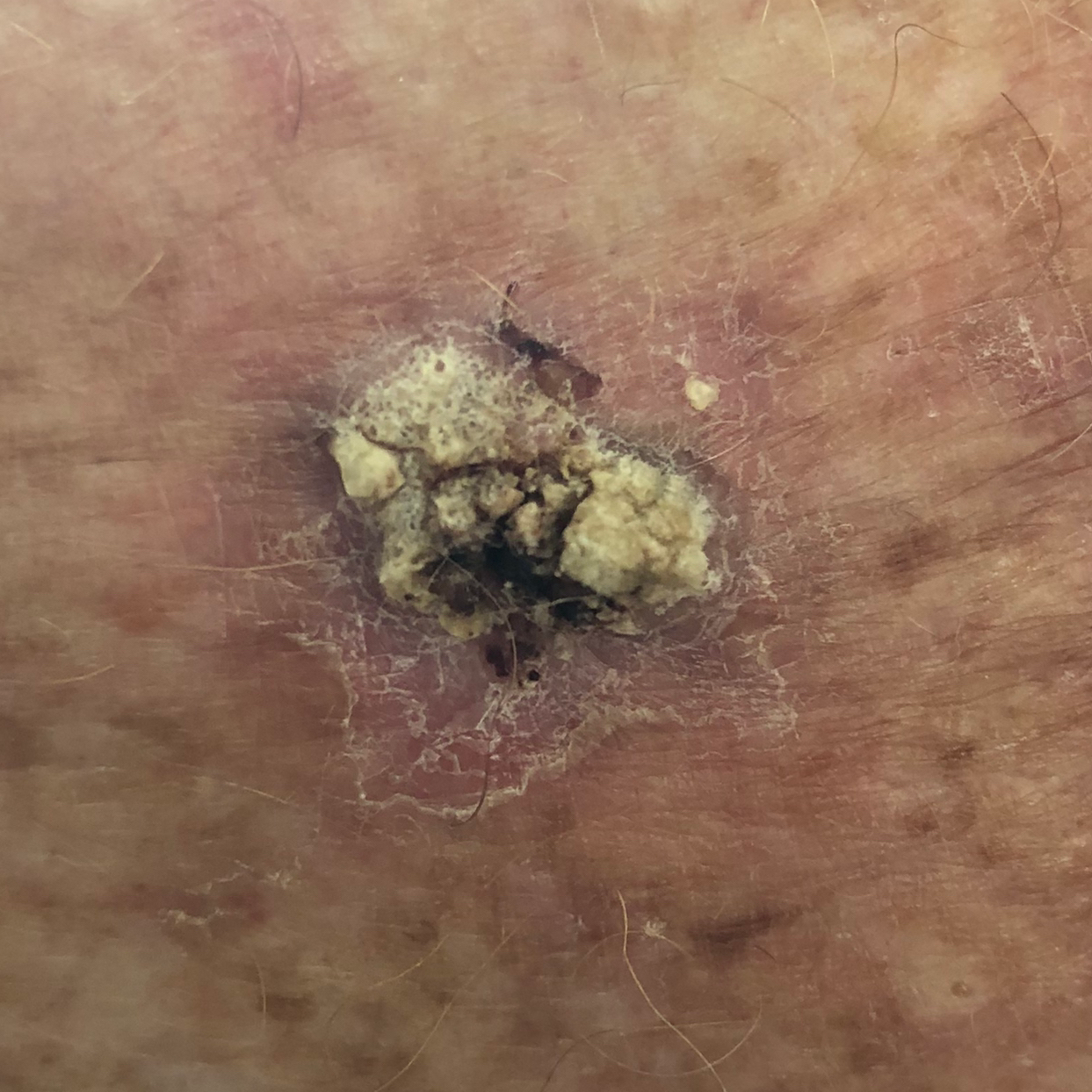A clinical photo of a skin lesion taken with a smartphone. A female subject age 71. The patient was assessed as FST III. The chart notes no pesticide exposure and no prior malignancy (patient or family). The lesion is located on a thigh. The lesion is roughly 20 by 18 mm. Per patient report, the lesion is elevated, itches, and hurts. Histopathology confirmed an actinic keratosis.